A subject in their 60s — 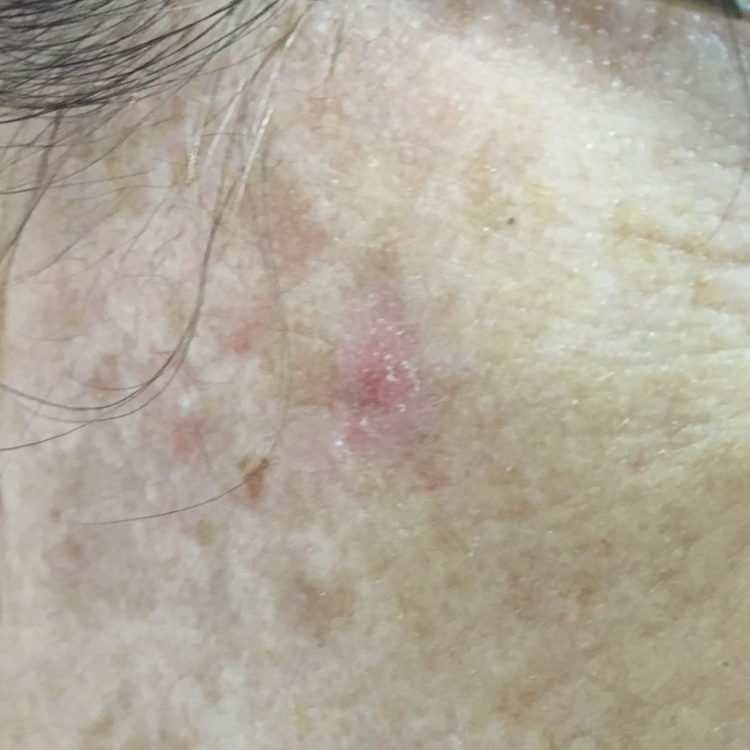  symptoms:
    present:
      - growth
      - itching
  diagnosis:
    name: actinic keratosis
    code: ACK
    malignancy: indeterminate
    confirmation: clinical consensus